A skin lesion imaged with a dermatoscope:
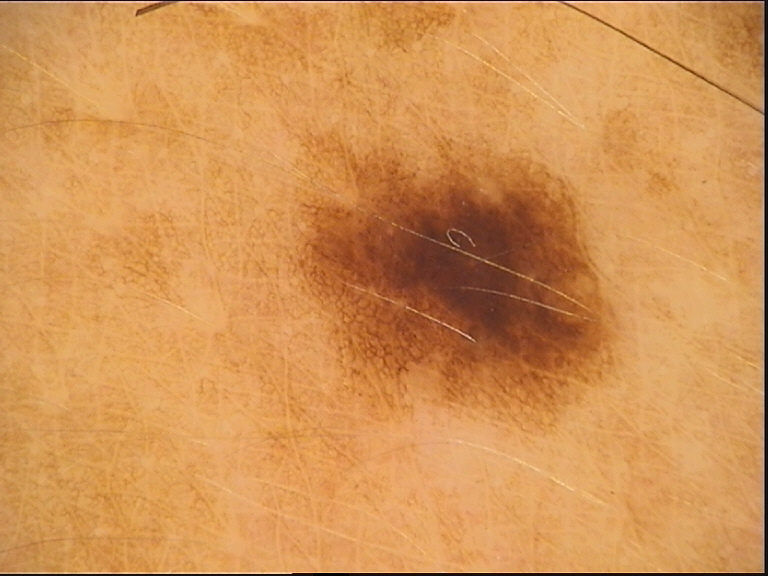<lesion>
  <diagnosis>
    <name>dysplastic junctional nevus</name>
    <code>jd</code>
    <malignancy>benign</malignancy>
    <super_class>melanocytic</super_class>
    <confirmation>expert consensus</confirmation>
  </diagnosis>
</lesion>